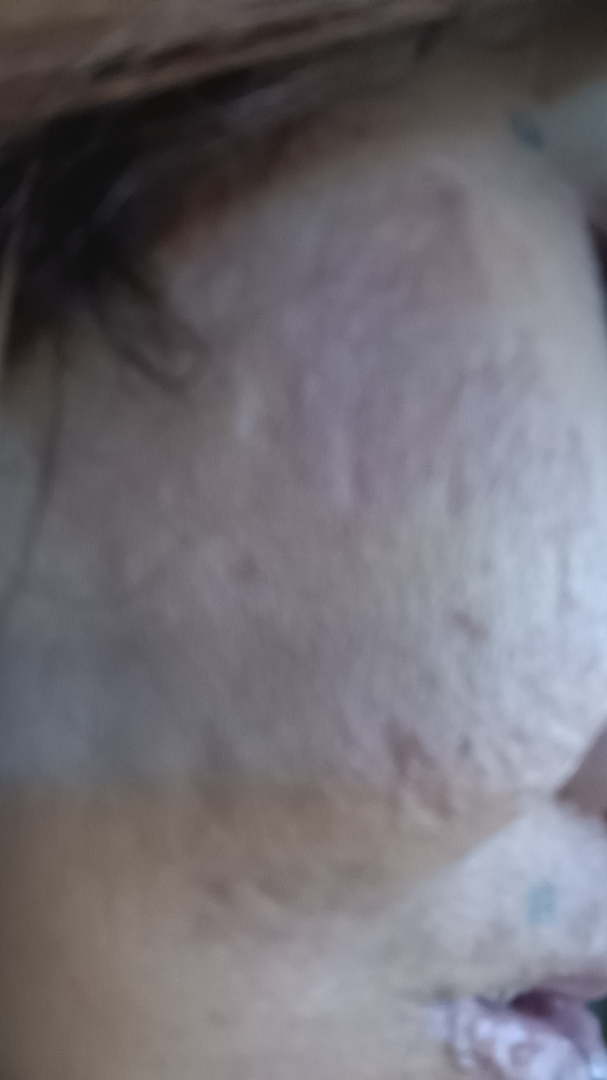Background:
The subject is female. The affected area is the head or neck. Reported duration is more than five years. The lesion is associated with enlargement, itching and bothersome appearance. The patient also reports shortness of breath. The photograph is a close-up of the affected area. The patient described the issue as acne. The patient notes the lesion is rough or flaky, raised or bumpy and fluid-filled. FST IV.
Findings:
Melasma, Scar Condition and Post-Inflammatory hyperpigmentation were considered with similar weight.